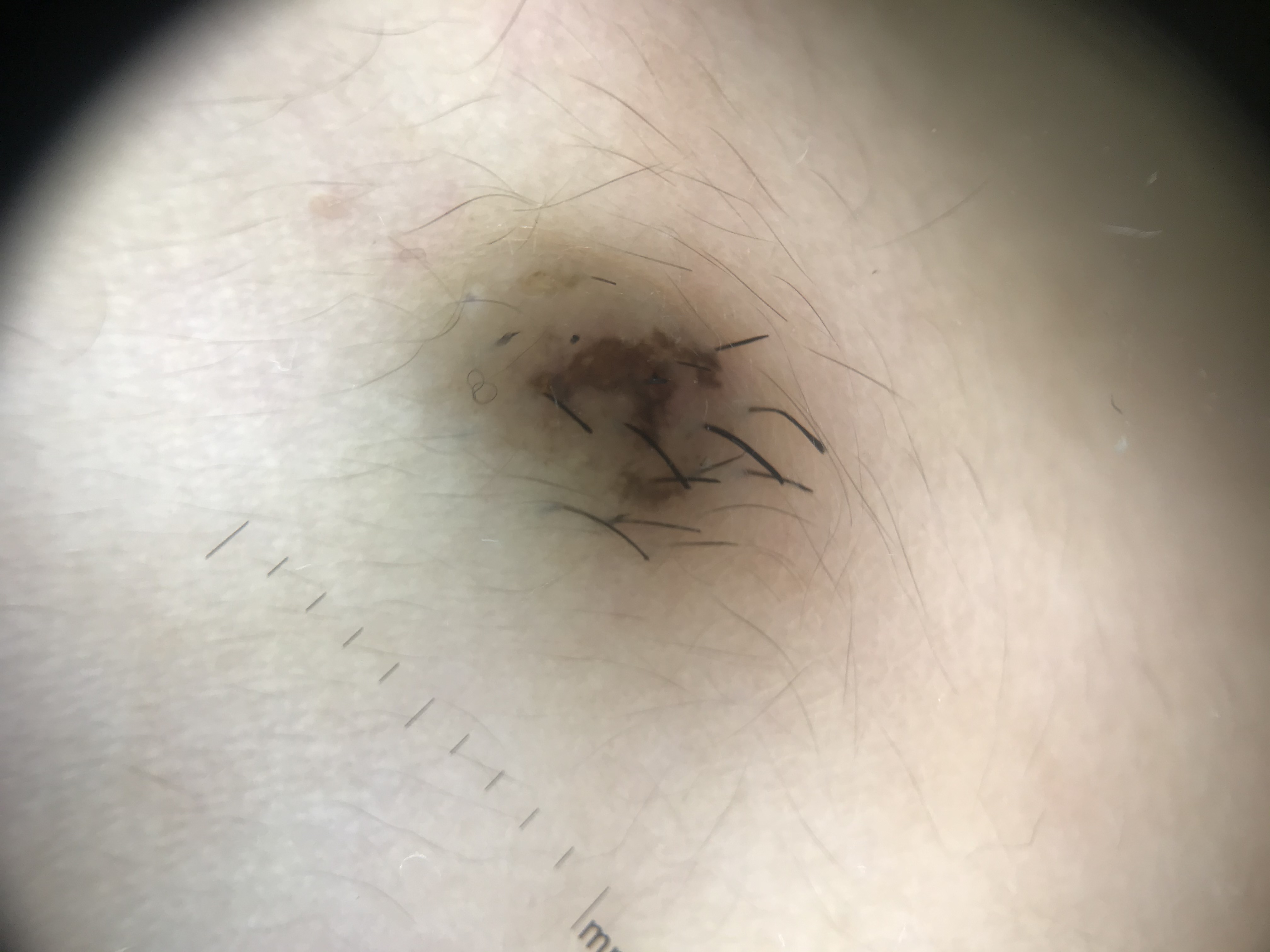Findings:
- diagnosis · Miescher nevus (expert consensus)